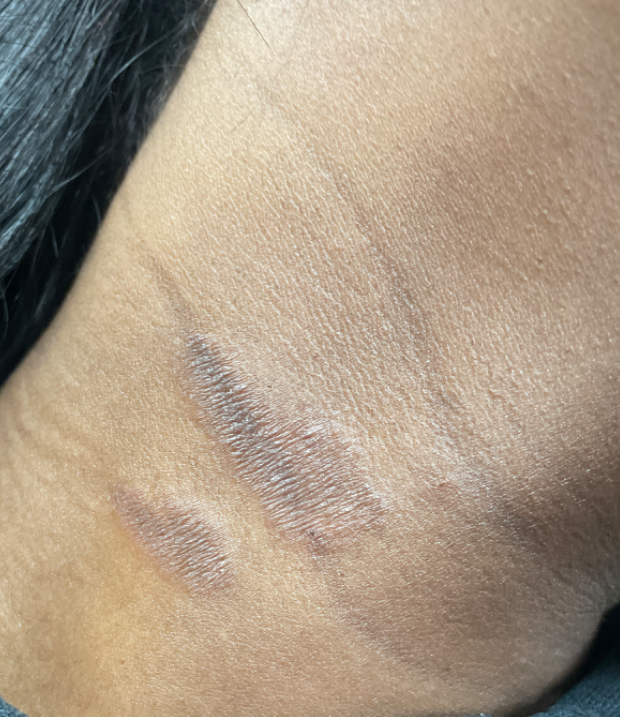The lesion involves the head or neck. This is a close-up image. Most consistent with Irritant Contact Dermatitis; also on the differential is Allergic Contact Dermatitis.